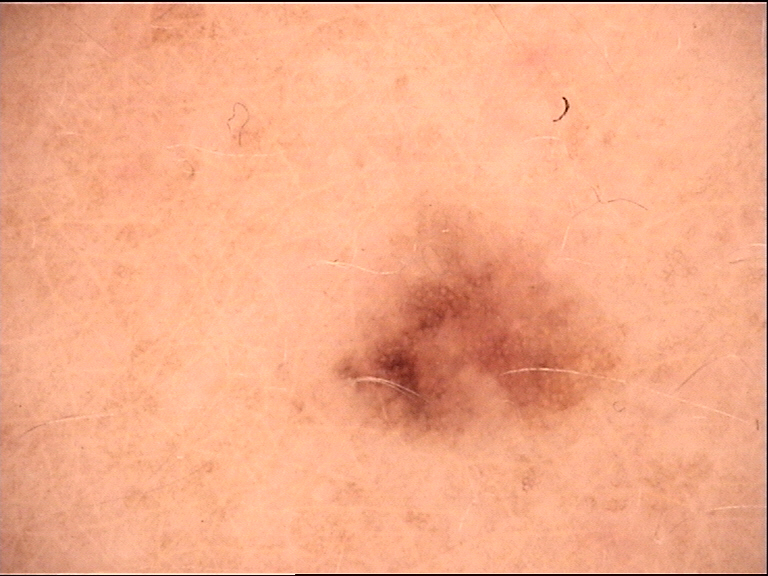The diagnostic label was a benign lesion — a dysplastic junctional nevus.